A close-up photograph, the head or neck is involved:
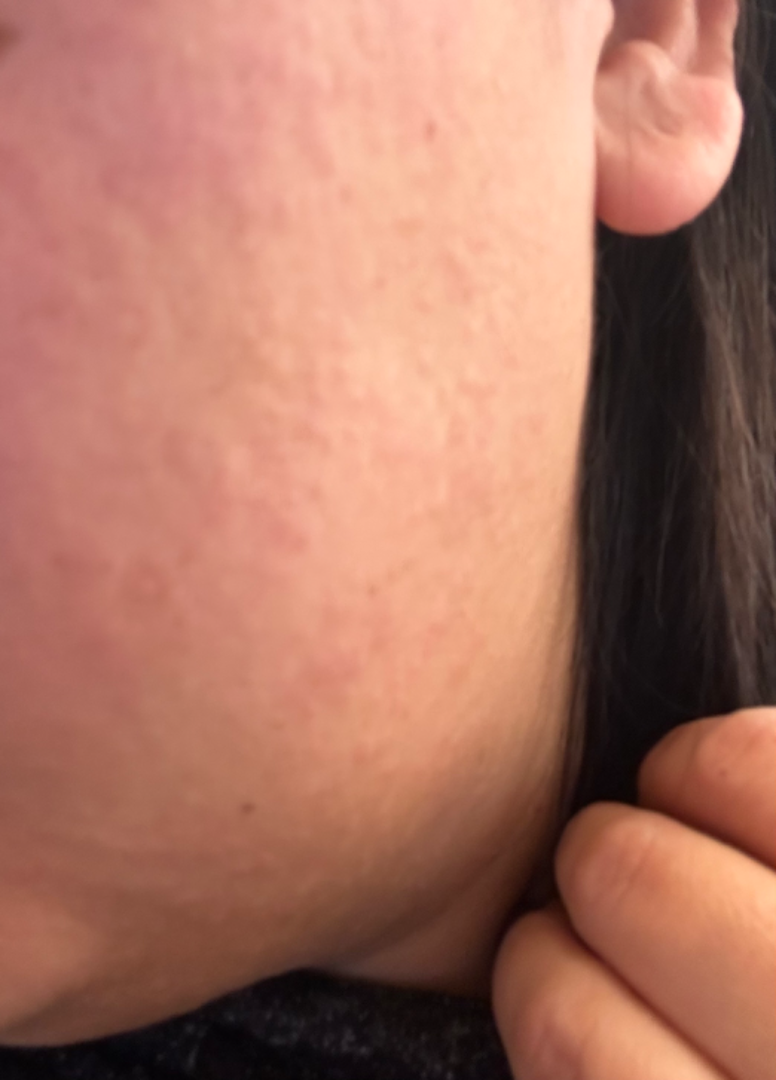Texture is reported as raised or bumpy. The patient described the issue as a rash. Reported lesion symptoms include itching and burning. No relevant systemic symptoms. On remote review of the image: Rosacea (favored); Irritant Contact Dermatitis (possible).